A clinical close-up photograph of a skin lesion. A female subject 57 years of age. The chart notes prior skin cancer (patient or family) and pesticide exposure. The patient was assessed as Fitzpatrick skin type III.
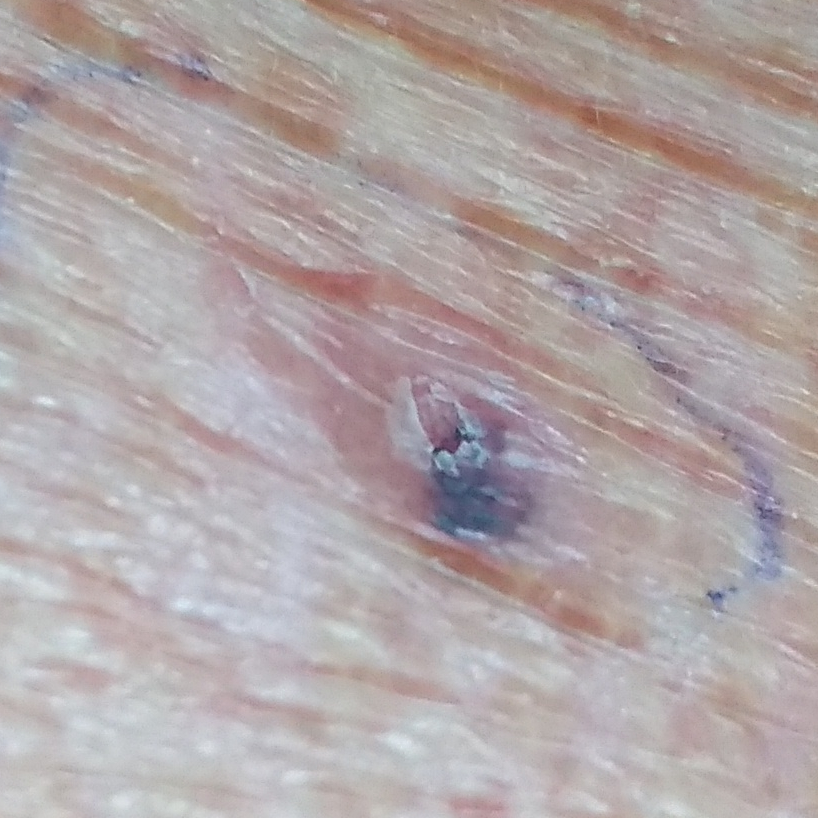The lesion was found on the chest.
The lesion measures approximately 10 × 5 mm.
The patient reports that the lesion has changed, has bled, has grown, and is elevated.
Confirmed on histopathology as a basal cell carcinoma.